Collected as part of a research study, without a referral diagnosis · the patient says their skin tans without first burning: 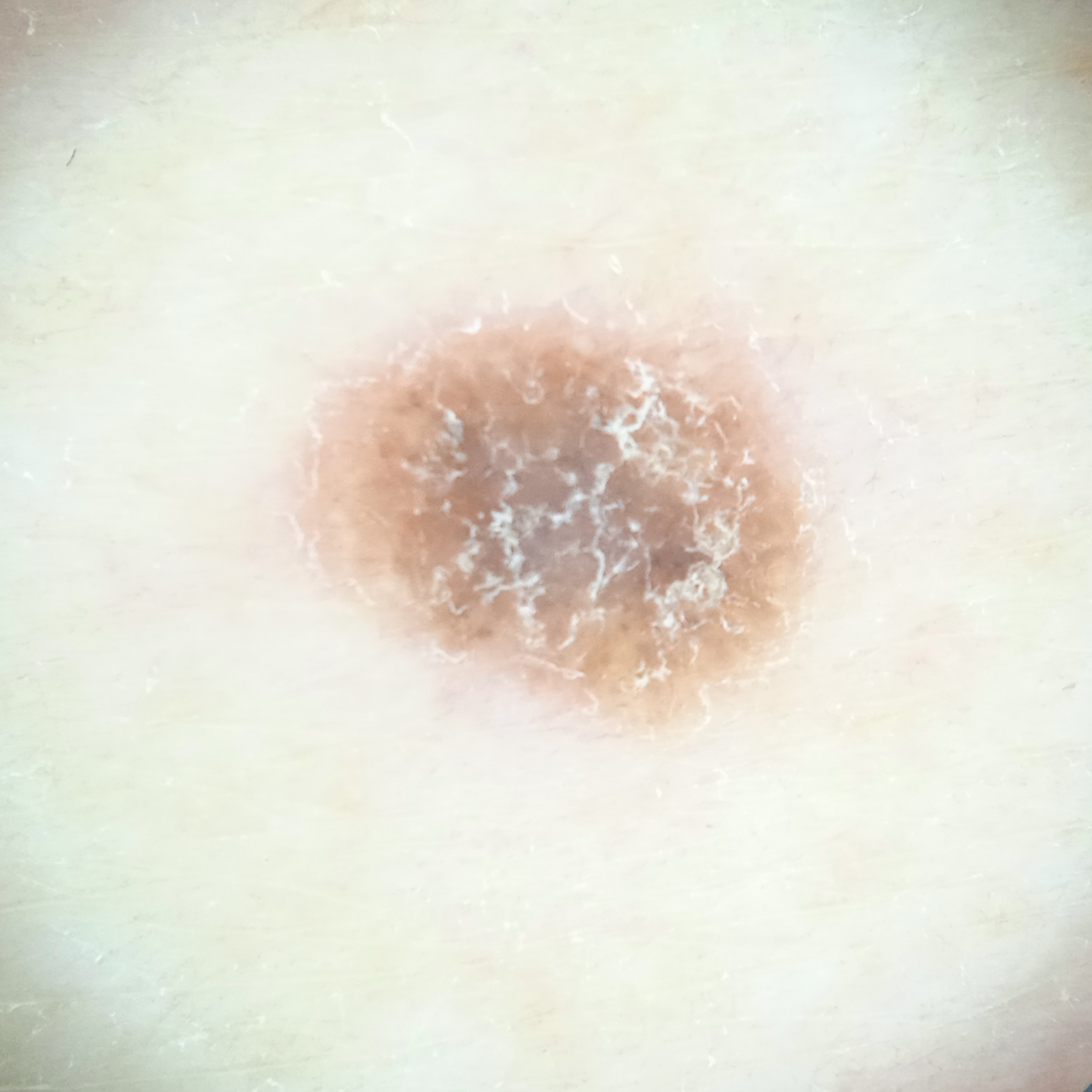Measuring roughly 5.9 mm.
The consensus diagnosis for this lesion was a seborrheic keratosis.